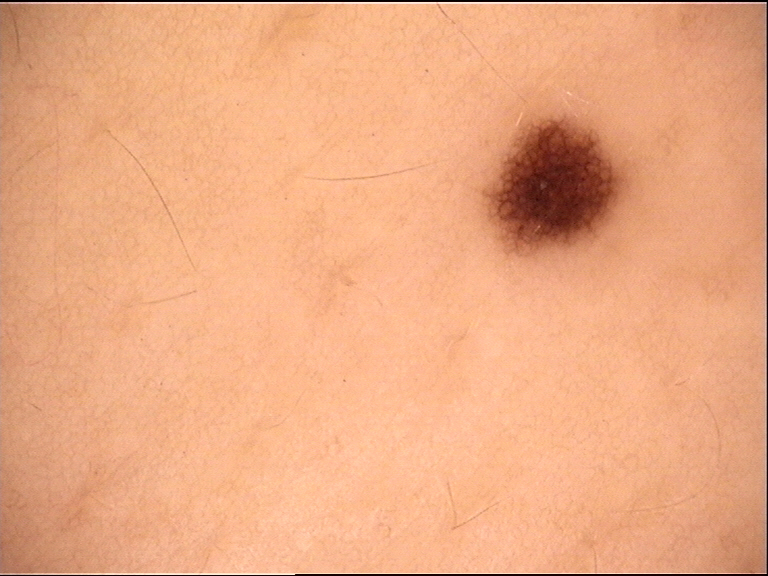lesion type=banal; label=junctional nevus (expert consensus).